Recorded as FST II; a female subject in their 70s; a skin lesion imaged with contact-polarized dermoscopy — 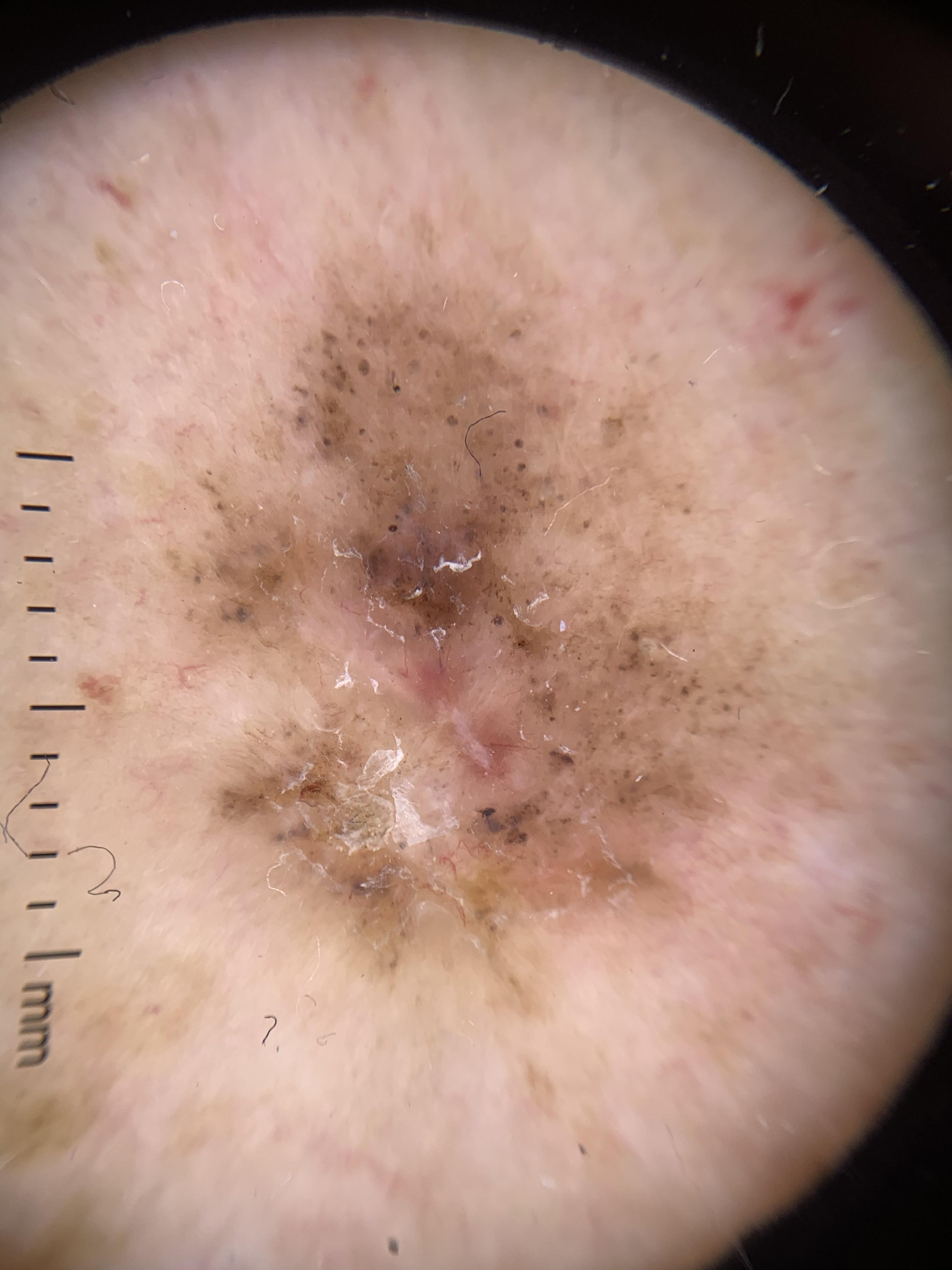Q: What is the anatomic site?
A: the lateral trunk
Q: What is the diagnosis?
A: Basal cell carcinoma (biopsy-proven)